The lesion involves the arm; this is a close-up image — 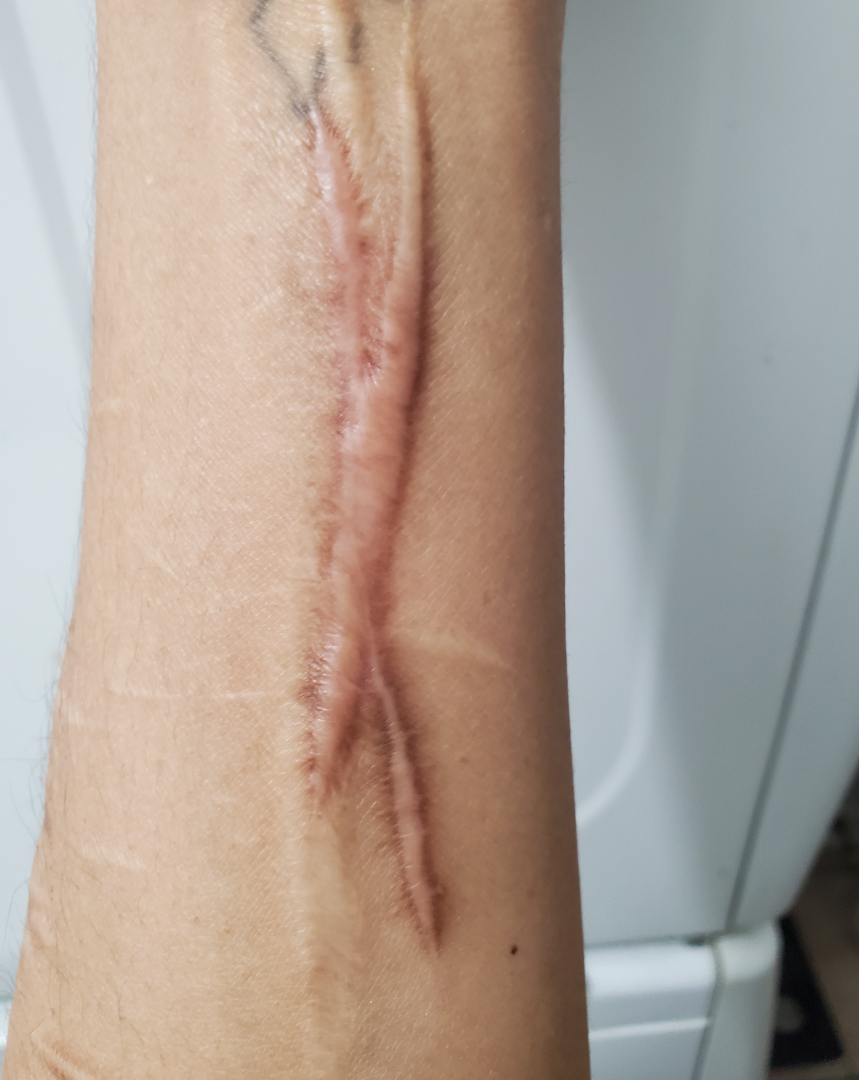On independent review by the dermatologists, in keeping with Scar Condition.